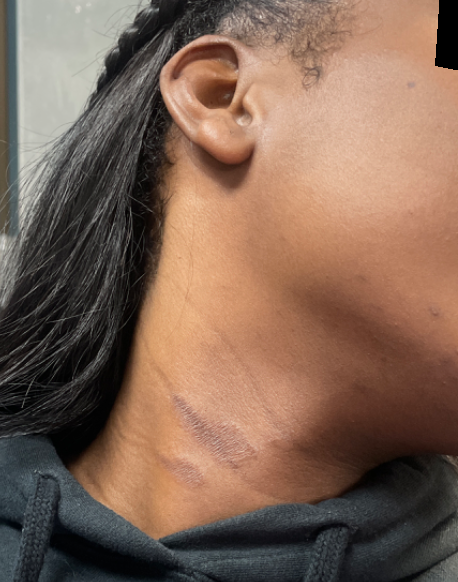location — head or neck
view — at an angle
differential — most consistent with Irritant Contact Dermatitis; an alternative is Allergic Contact Dermatitis